A dermoscopic photograph of a skin lesion.
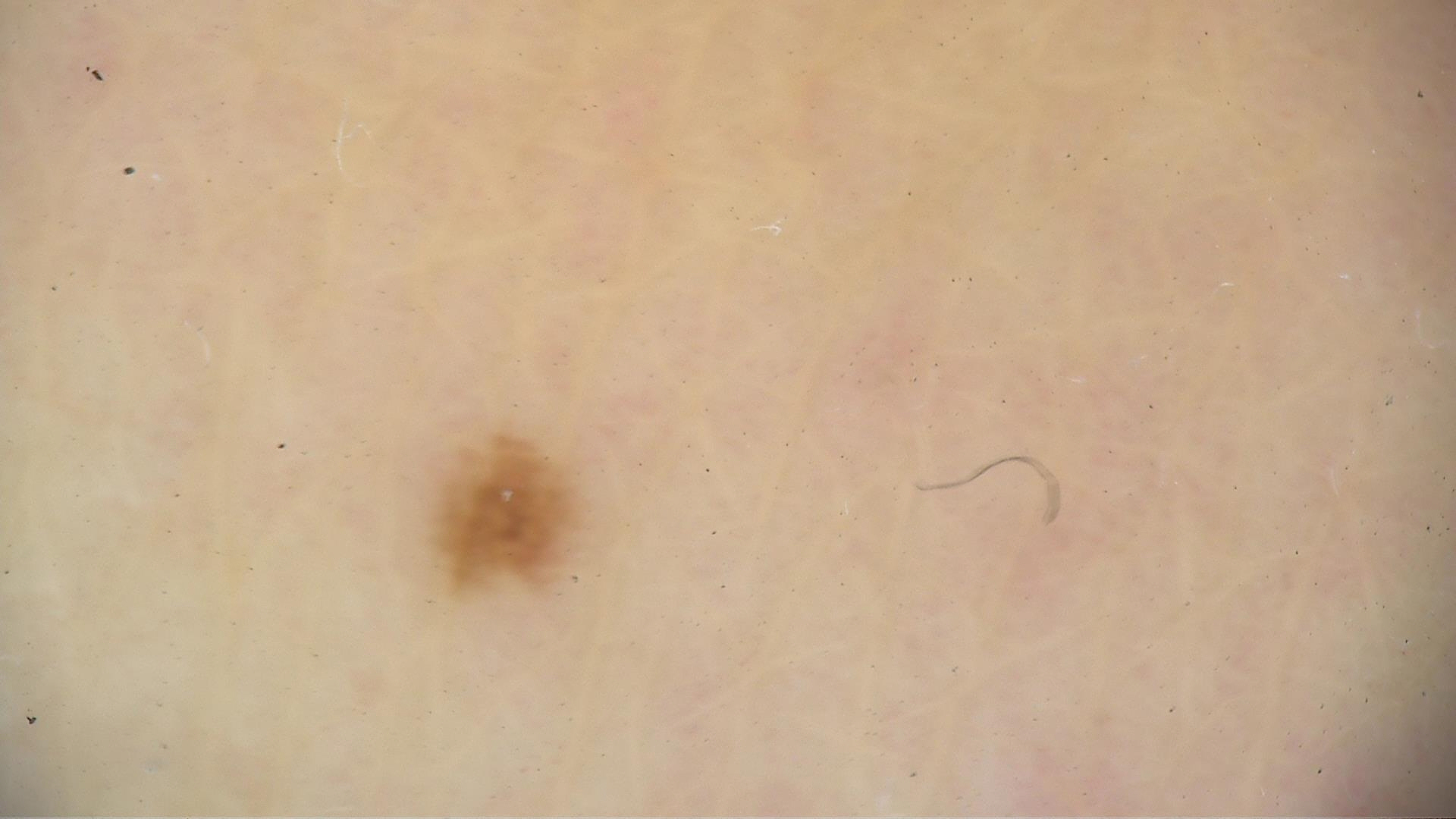- class: acral dysplastic junctional nevus (expert consensus)